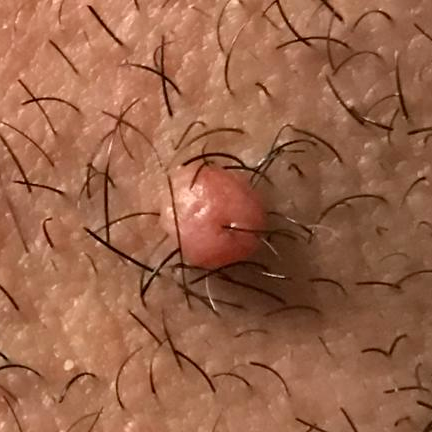patient=aged 43
image=clinical photo
site=the face
reported symptoms=growth, elevation
diagnosis=nevus (clinical consensus)